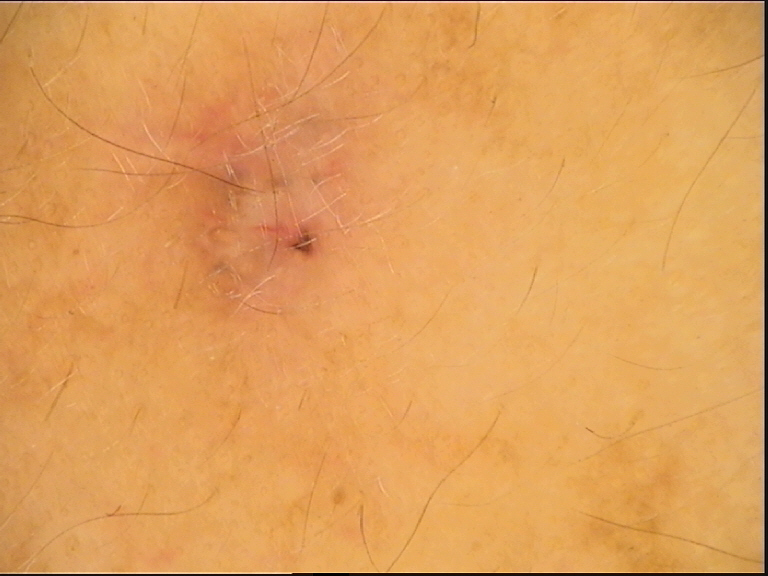A dermoscopic photograph of a skin lesion. Confirmed on histopathology as a basal cell carcinoma.